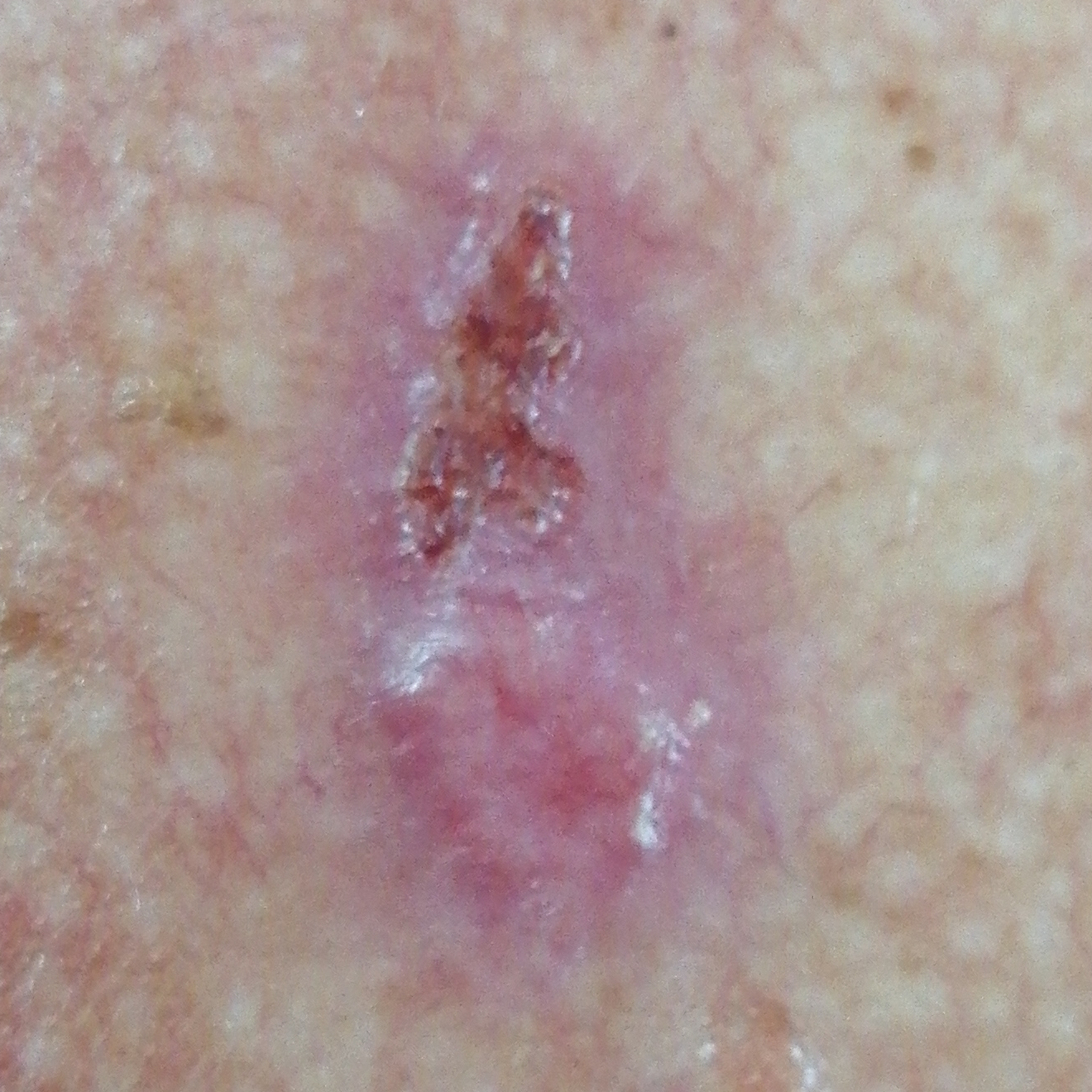Findings: FST II. A clinical photograph showing a skin lesion. A male patient 72 years old. The lesion is located on the back. Measuring about 22 × 11 mm. The patient describes that the lesion hurts, itches, is elevated, and has bled. Conclusion: Confirmed on histopathology as a basal cell carcinoma.